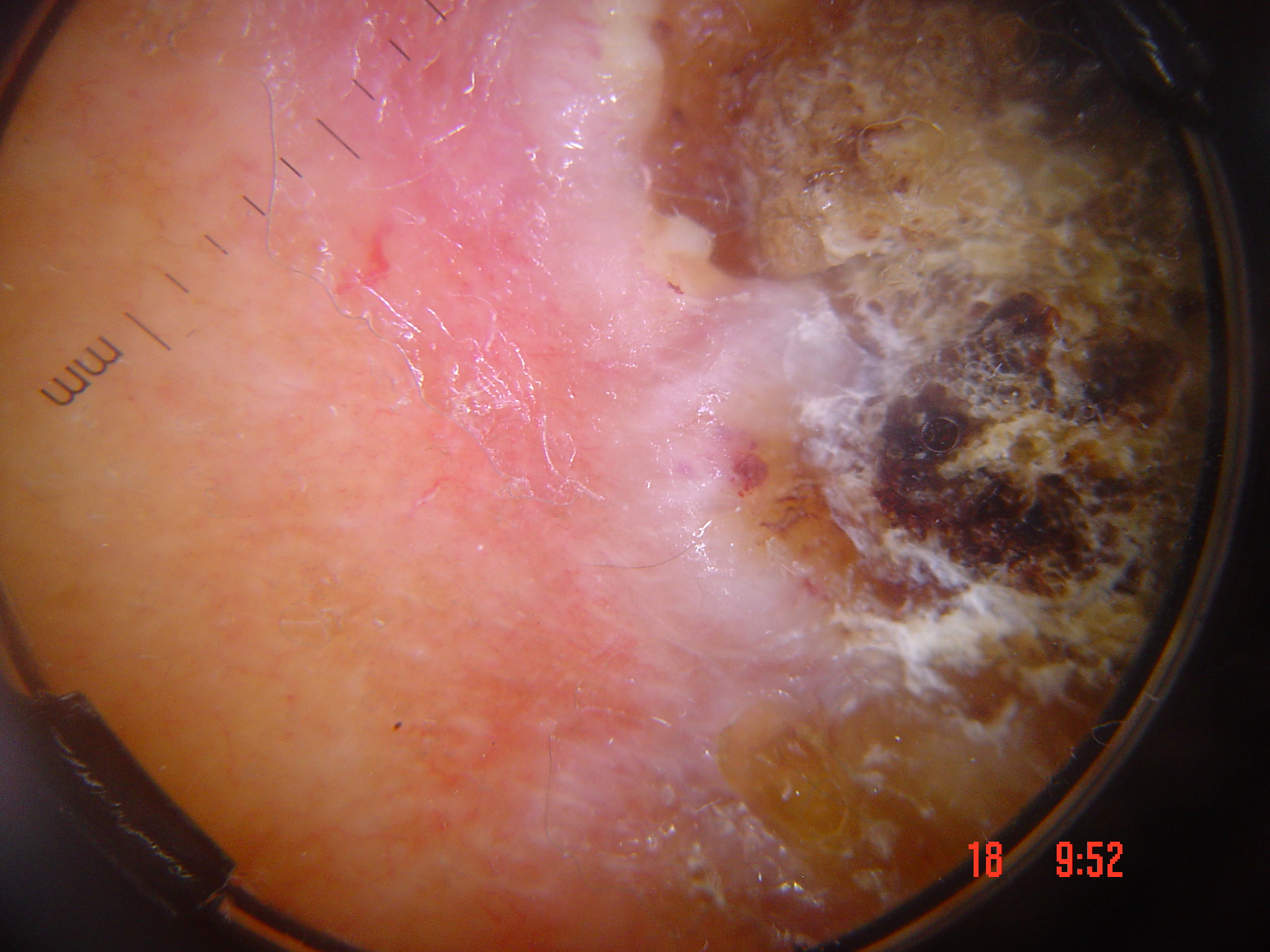A dermoscopy image of a single skin lesion.
This is a keratinocytic lesion.
Histopathology confirmed a squamous cell carcinoma.